The chart records prior skin cancer (patient or family), no alcohol use, and no tobacco use · a female subject 67 years of age · the patient is Fitzpatrick II · a clinical photograph showing a skin lesion: 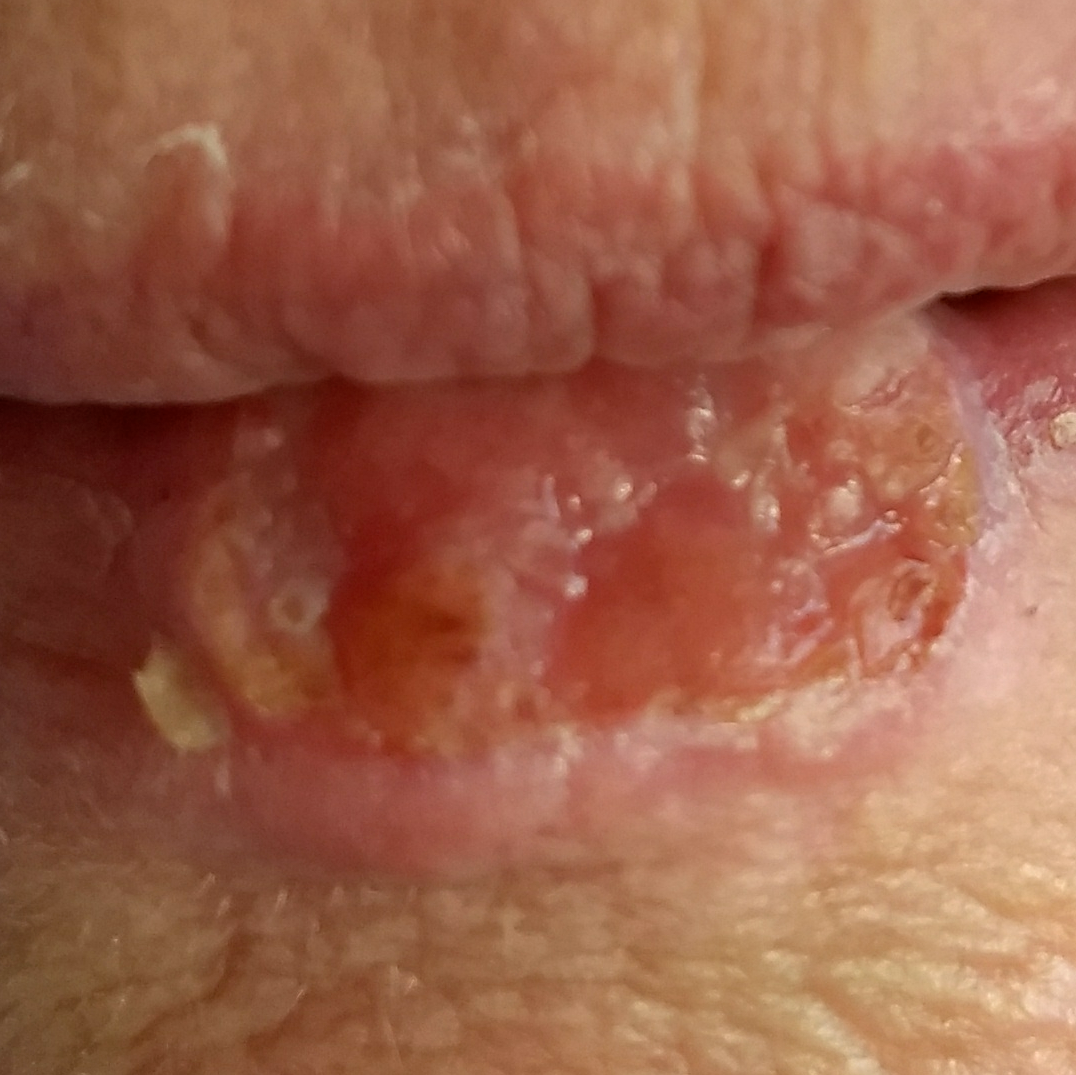Findings:
– location · a lip
– lesion diameter · 17x15 mm
– patient-reported symptoms · elevation, growth, bleeding, pain, itching / no change in appearance
– diagnosis · squamous cell carcinoma (biopsy-proven)